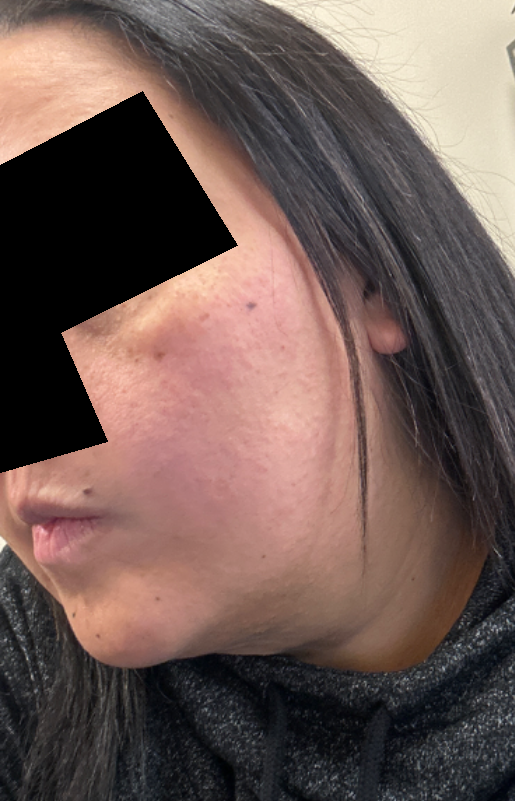symptoms: itching and burning | skin tone: Fitzpatrick phototype IV; lay reviewers estimated Monk skin tone scale 3 (US pool) or 2 (India pool) | duration: less than one week | lesion texture: raised or bumpy | site: head or neck | framing: at a distance | patient's own categorization: a rash | impression: most likely Rosacea; with consideration of Irritant Contact Dermatitis.